The photograph was taken at a distance · located on the front of the torso, arm and leg · female patient, age 18–29:
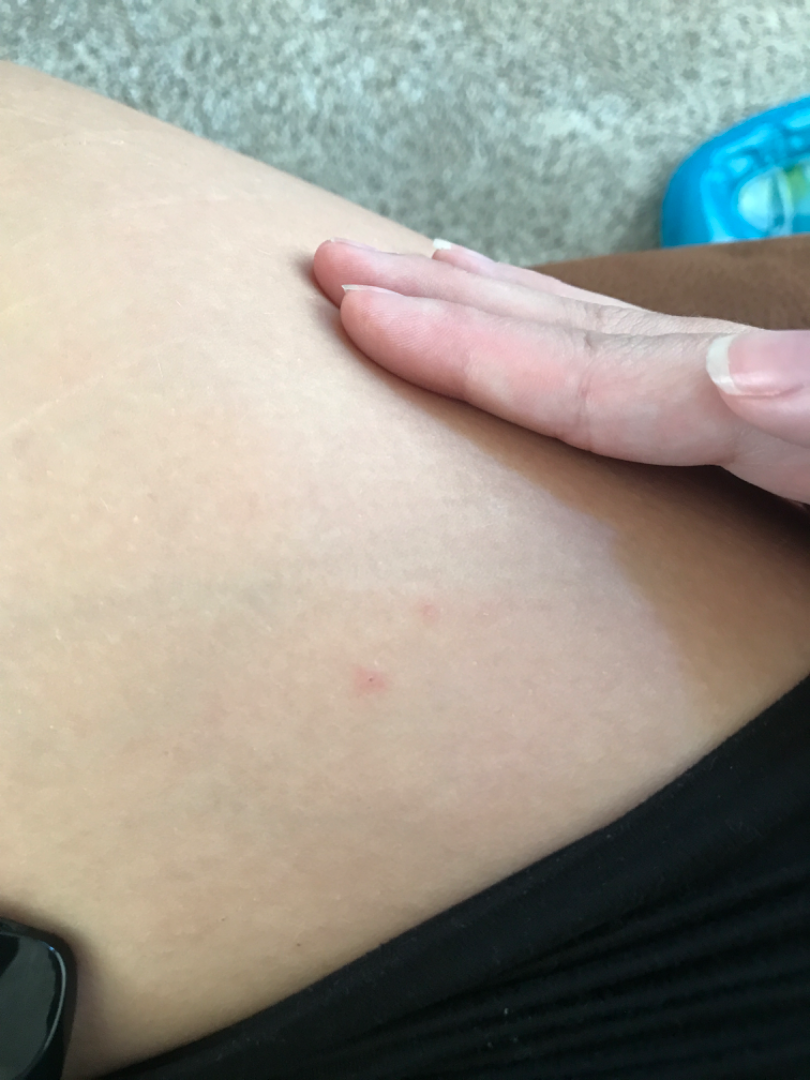Q: What is the differential diagnosis?
A: the primary impression is Eczema; also consider Scabies